A dermoscopy image of a single skin lesion. A male patient in their 50s.
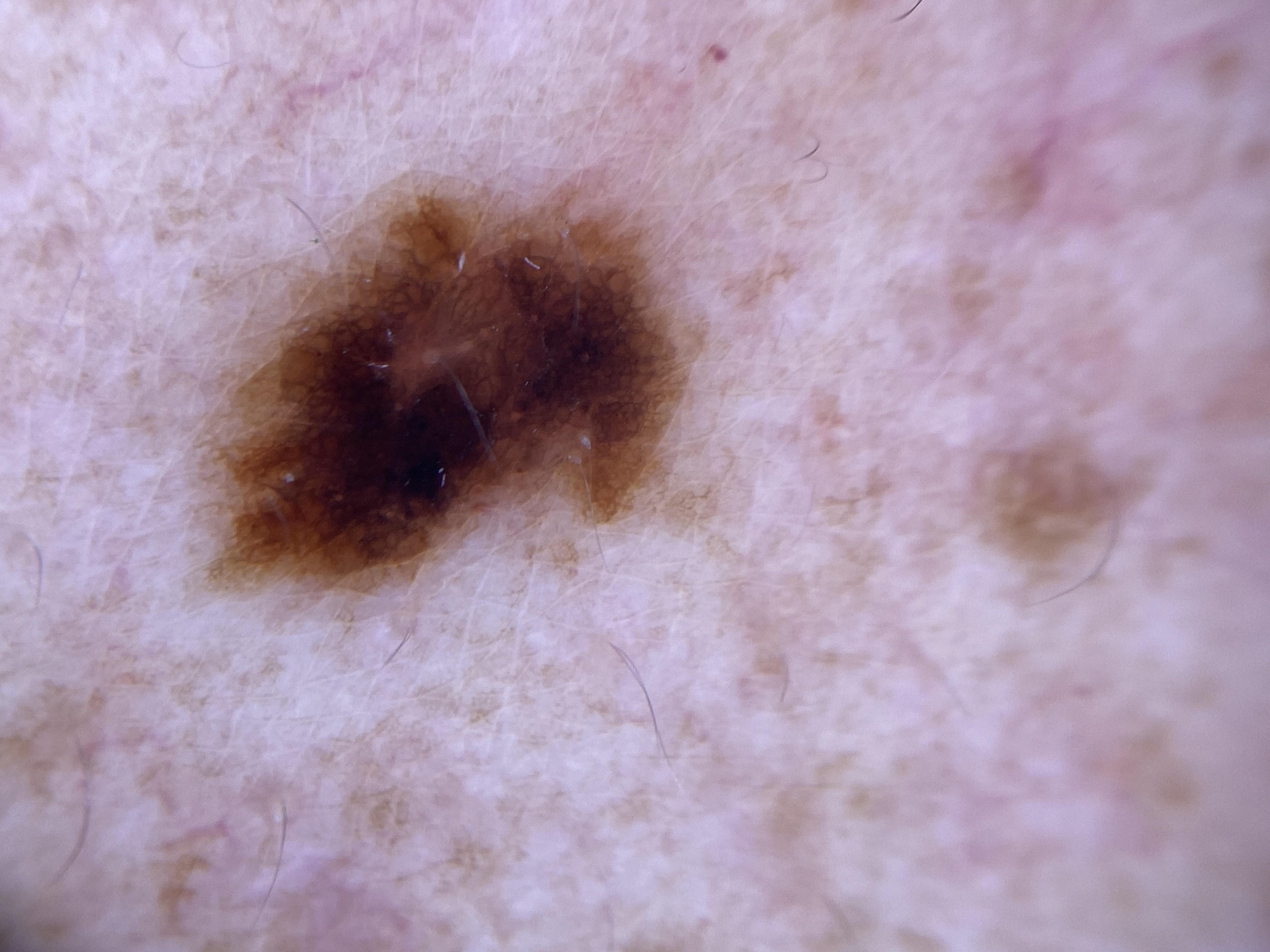The lesion involves the anterior trunk. Histopathologically confirmed as a nevus.